A dermoscopic image of a skin lesion.
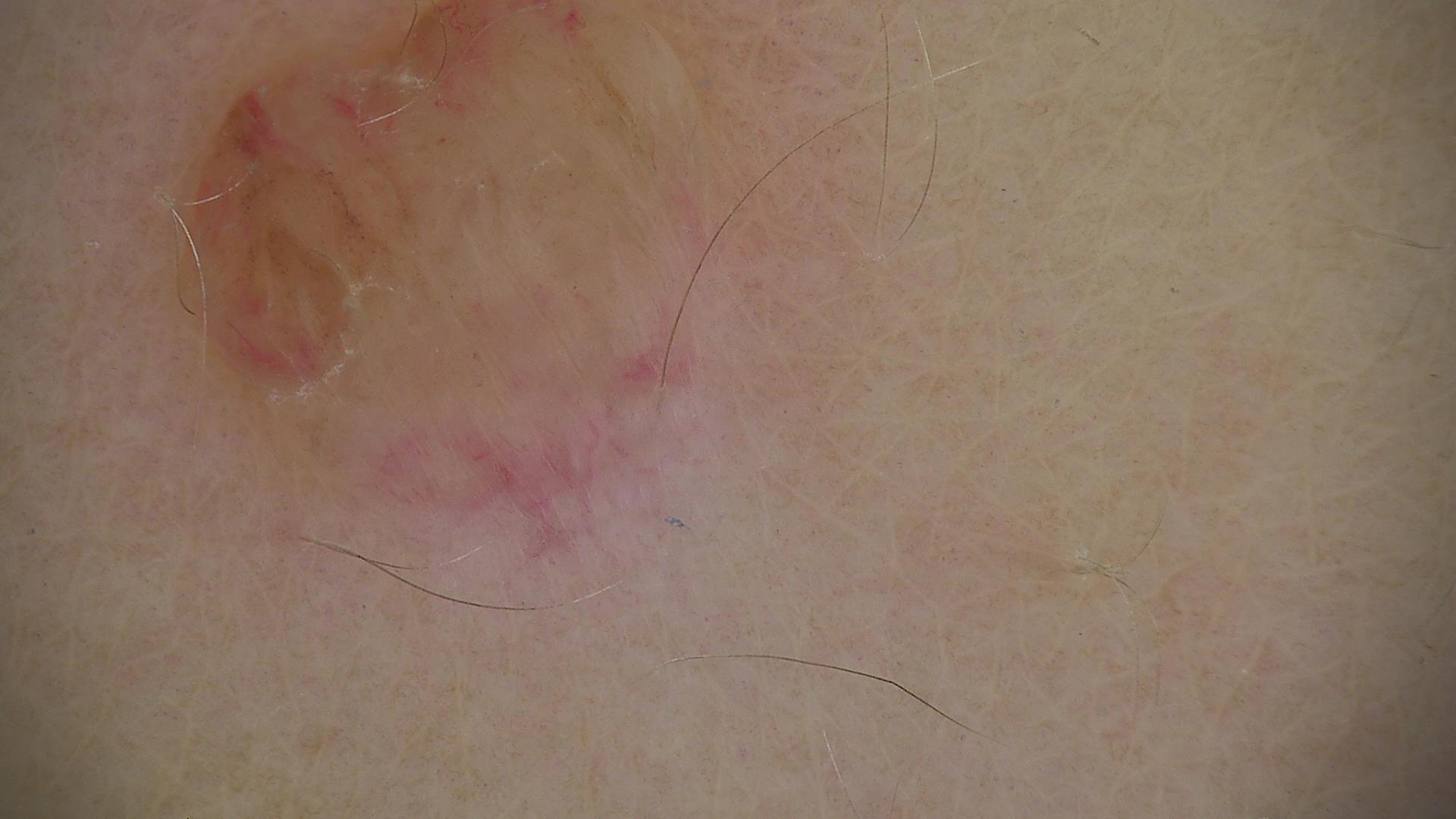category = banal, assessment = dermal nevus (expert consensus).